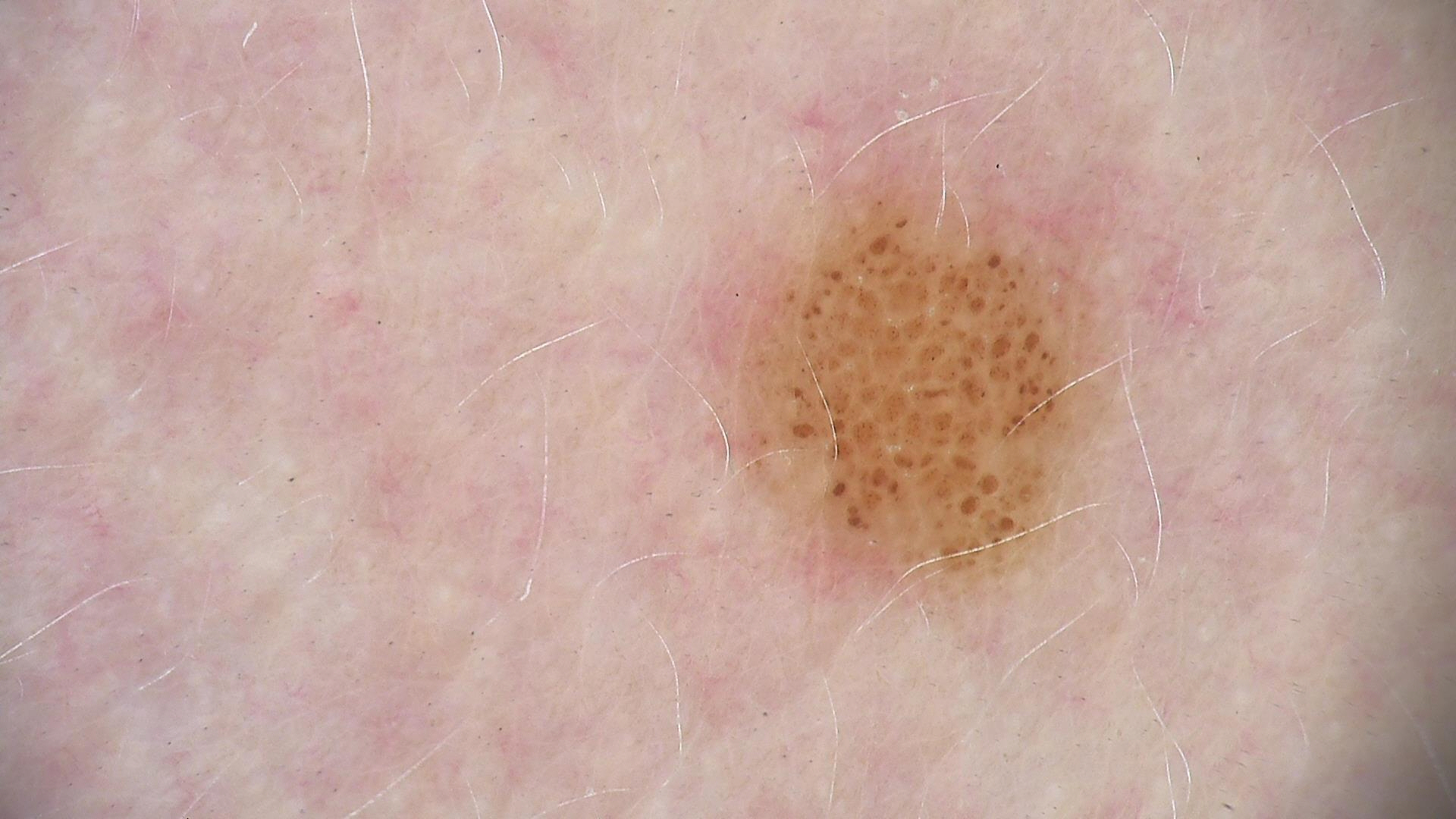- modality · dermatoscopy
- assessment · dysplastic junctional nevus (expert consensus)